The patient indicates the condition has been present for less than one week; associated systemic symptoms include joint pain, fatigue and shortness of breath; the photograph is a close-up of the affected area; skin tone: Fitzpatrick skin type III; the patient indicates itching and burning: 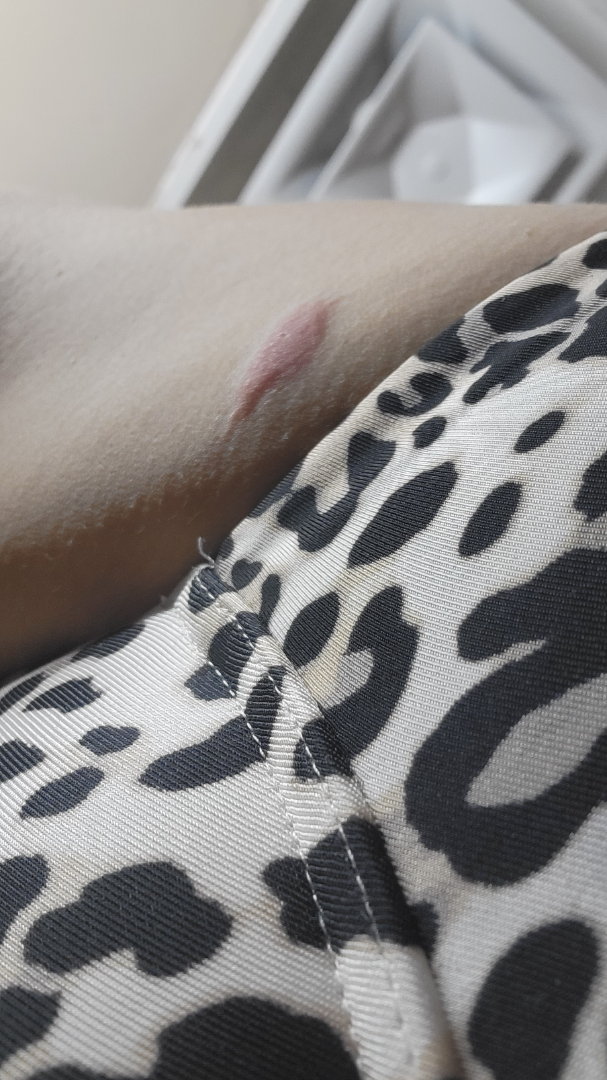<dermatology_case>
<assessment>not assessable</assessment>
</dermatology_case>